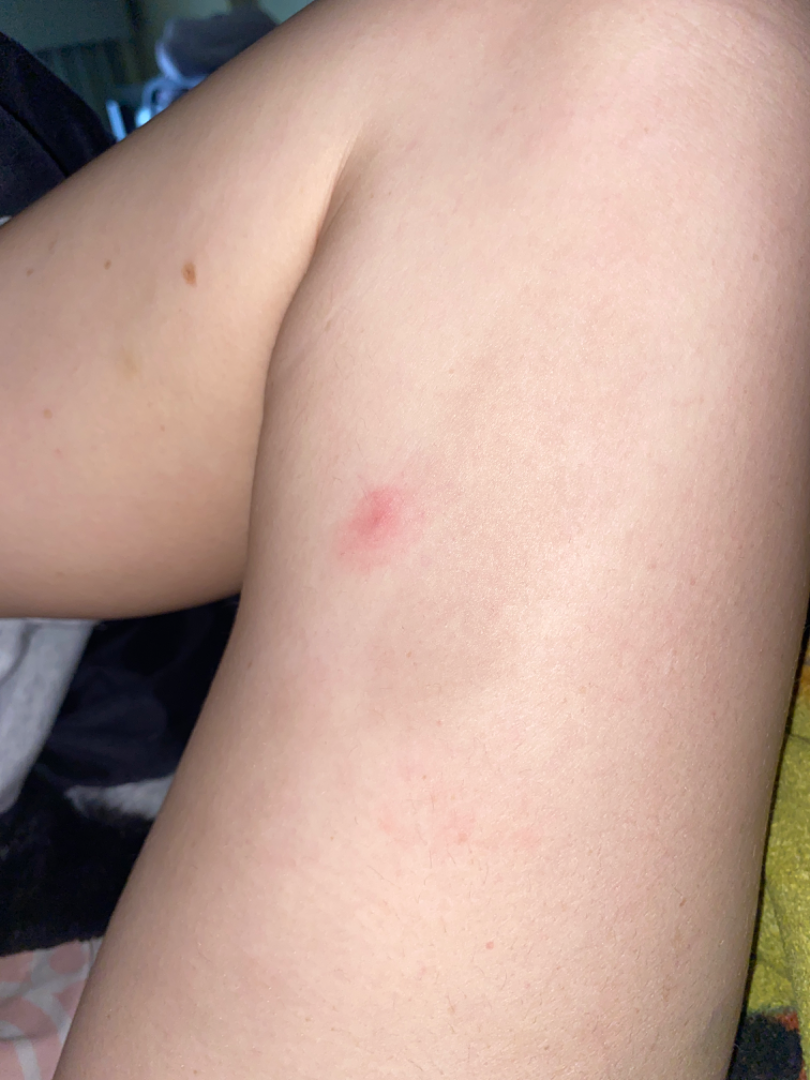assessment: indeterminate.